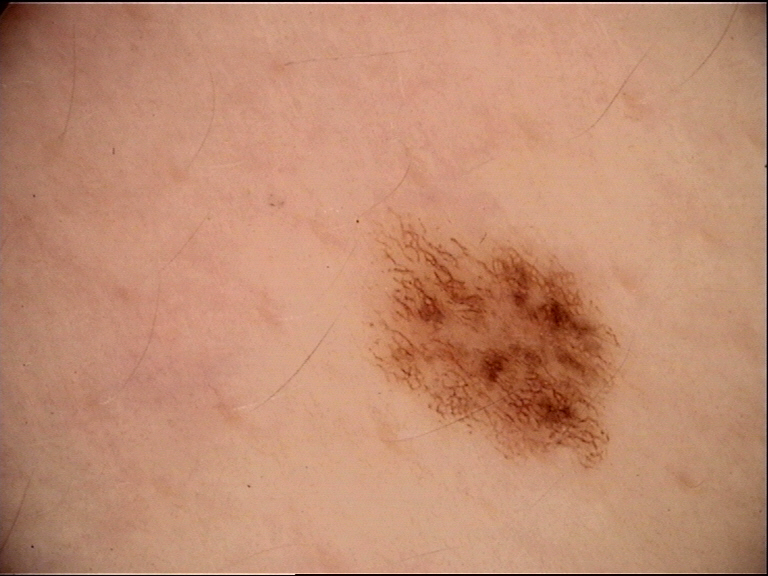* image: dermoscopy
* diagnostic label: dysplastic junctional nevus (expert consensus)